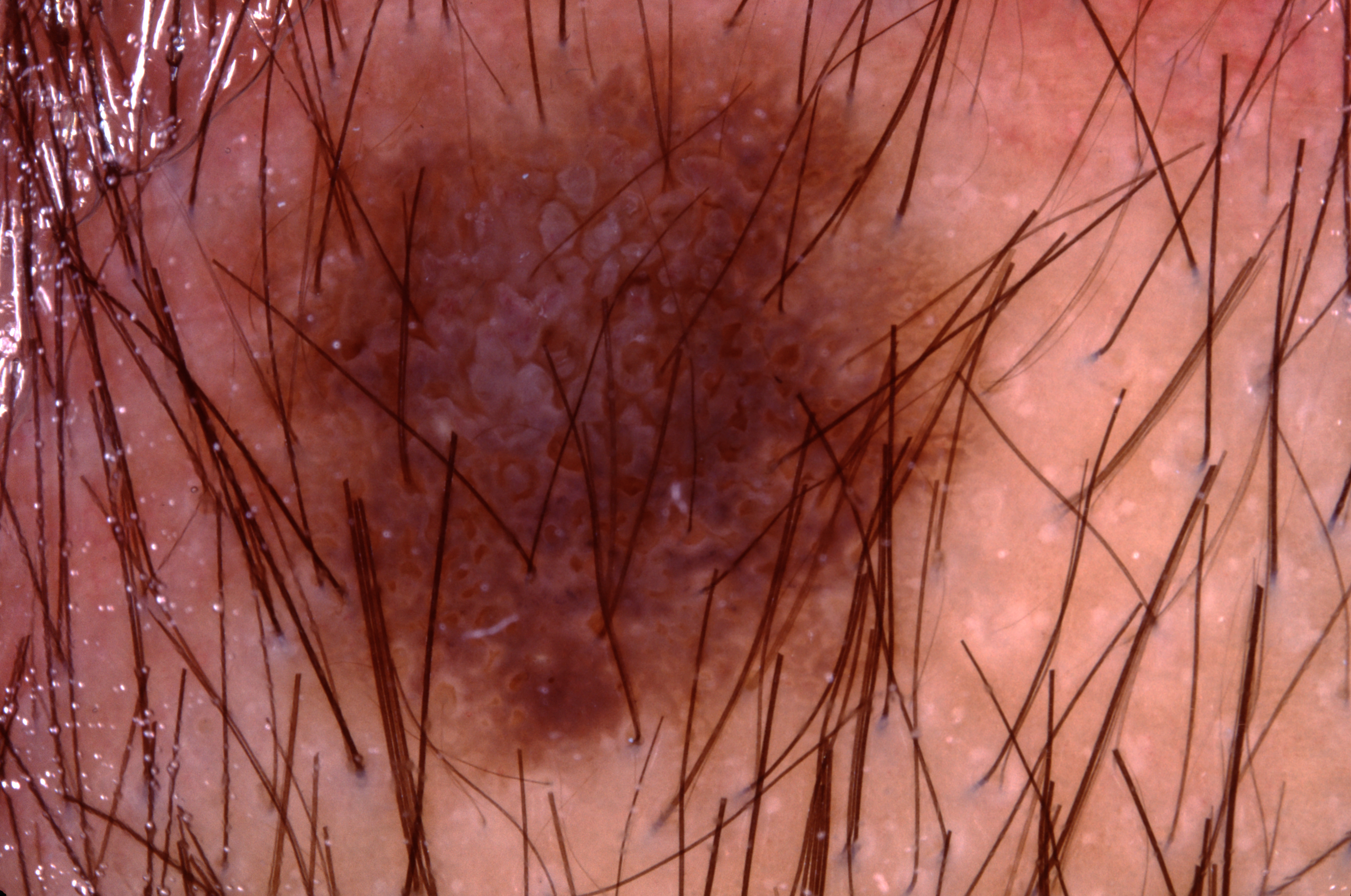The subject is a male aged around 40. A dermoscopy image of a single skin lesion. Dermoscopic examination shows milia-like cysts; no streaks, pigment network, or negative network. The lesion is bounded by bbox(169, 21, 1024, 798). Expert review diagnosed this as a seborrheic keratosis, a benign skin lesion.